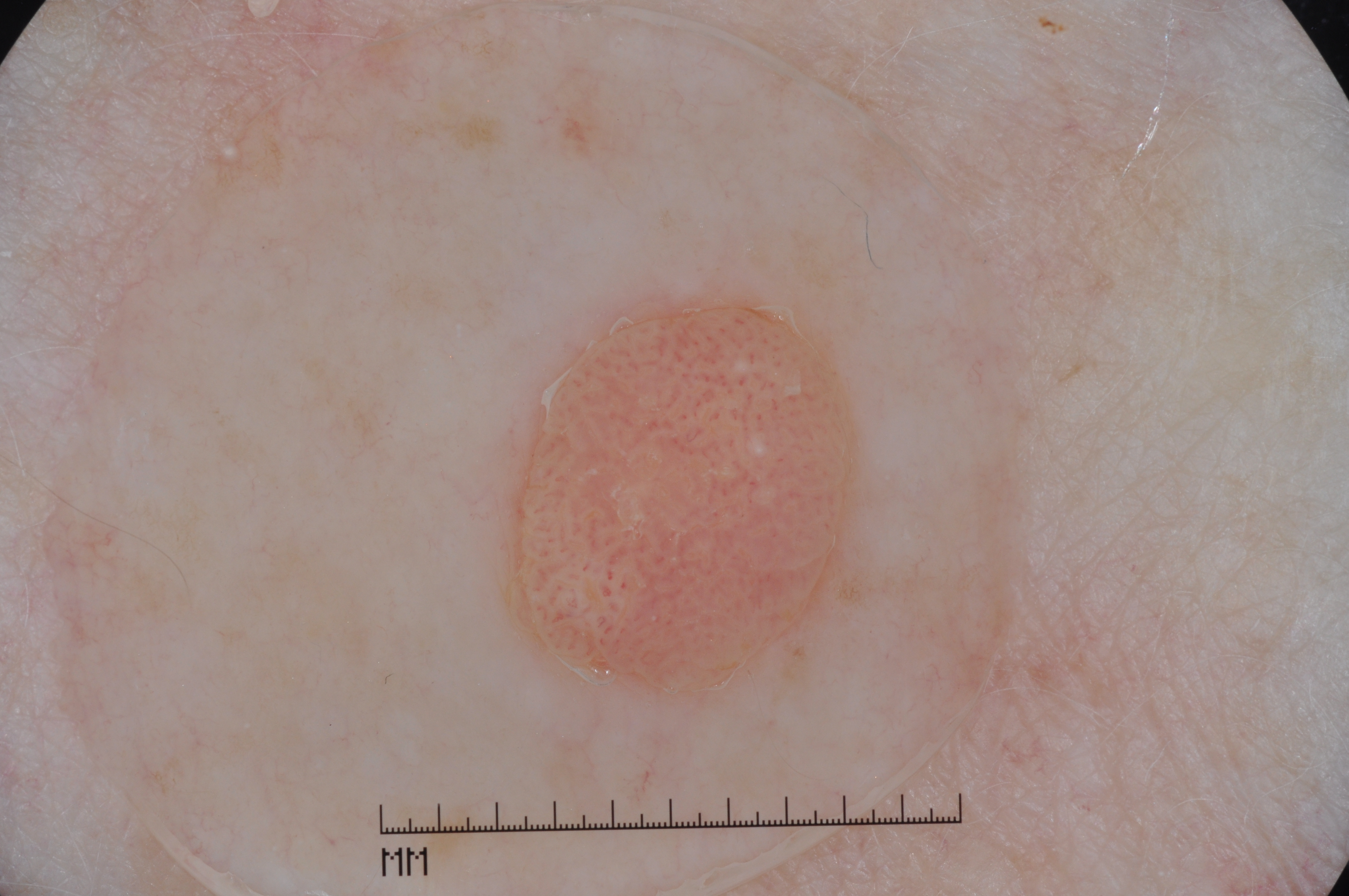A female patient in their mid- to late 70s.
Dermoscopy of a skin lesion.
On dermoscopy, the lesion shows milia-like cysts.
The lesion spans left=495, top=287, right=875, bottom=707.
A mid-sized lesion within the field.
Expert review diagnosed this as a seborrheic keratosis.